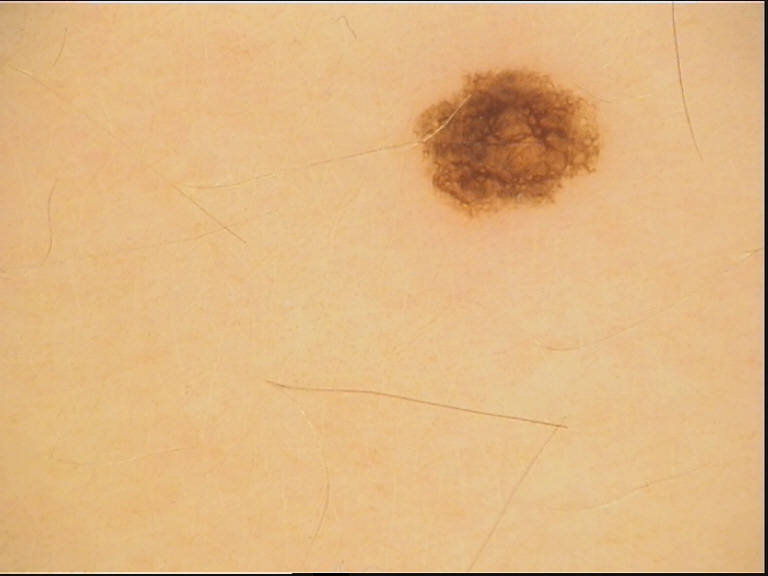A dermoscopic photograph of a skin lesion. Classified as a benign lesion — a dysplastic junctional nevus.